A patient aged 34 · a clinical close-up photograph of a skin lesion: 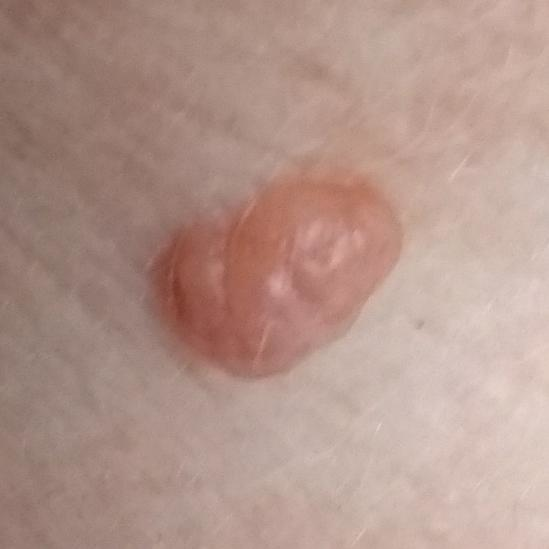The lesion is on the neck.
The patient reports that the lesion has grown and is elevated.
The consensus clinical diagnosis was a nevus.